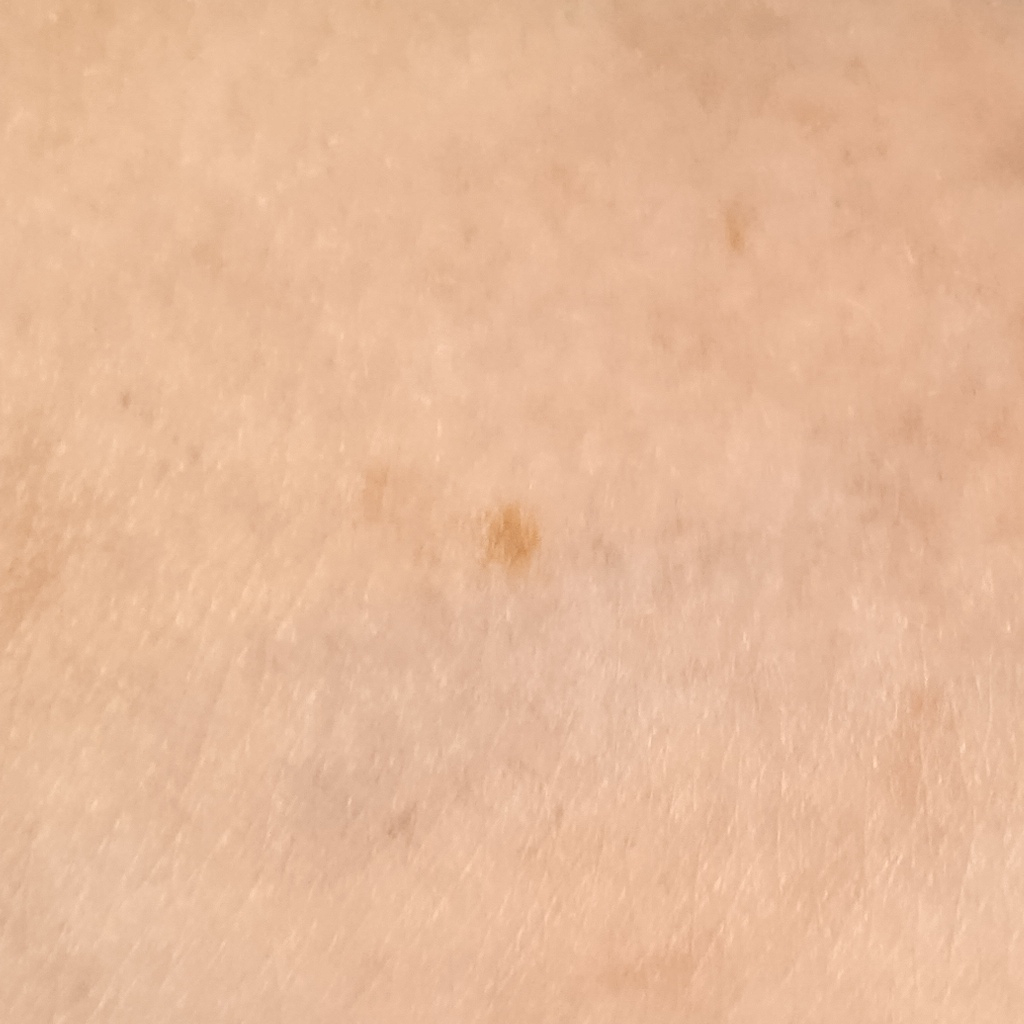A female patient age 59. The patient says their skin reddens with sun exposure. The patient describes having a moderate number of moles. The lesion is located on an arm. Measuring roughly 6.5 mm. The diagnostic impression was a melanocytic nevus.